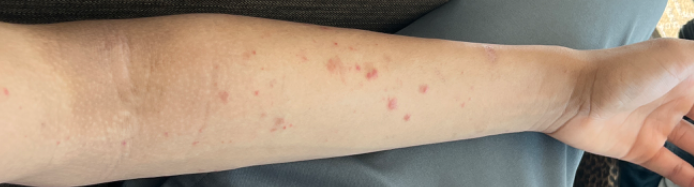Skin tone: Fitzpatrick skin type II.
The lesion involves the front of the torso, back of the torso, leg and arm.
The patient considered this acne.
Texture is reported as raised or bumpy.
The photograph was taken at a distance.
The subject is a male aged 18–29.
The lesion is associated with bothersome appearance and itching.
Present for one to three months.
Most consistent with Insect Bite; also on the differential is Allergic Contact Dermatitis; a more distant consideration is Eczema; less probable is Purpura; less likely is Folliculitis.